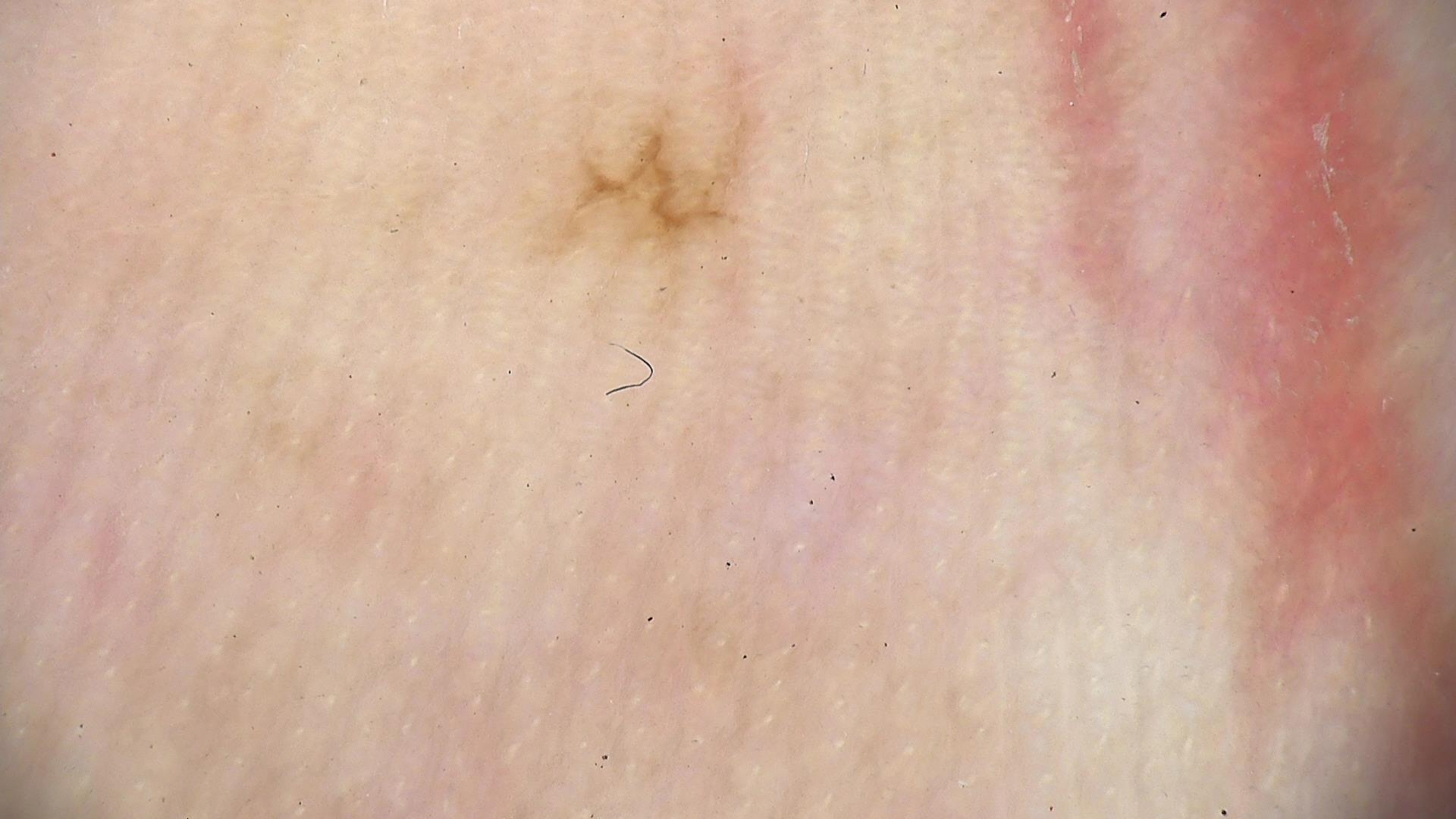diagnosis=acral dysplastic junctional nevus (expert consensus).